A skin lesion imaged with a dermatoscope, a female patient about 60 years old:
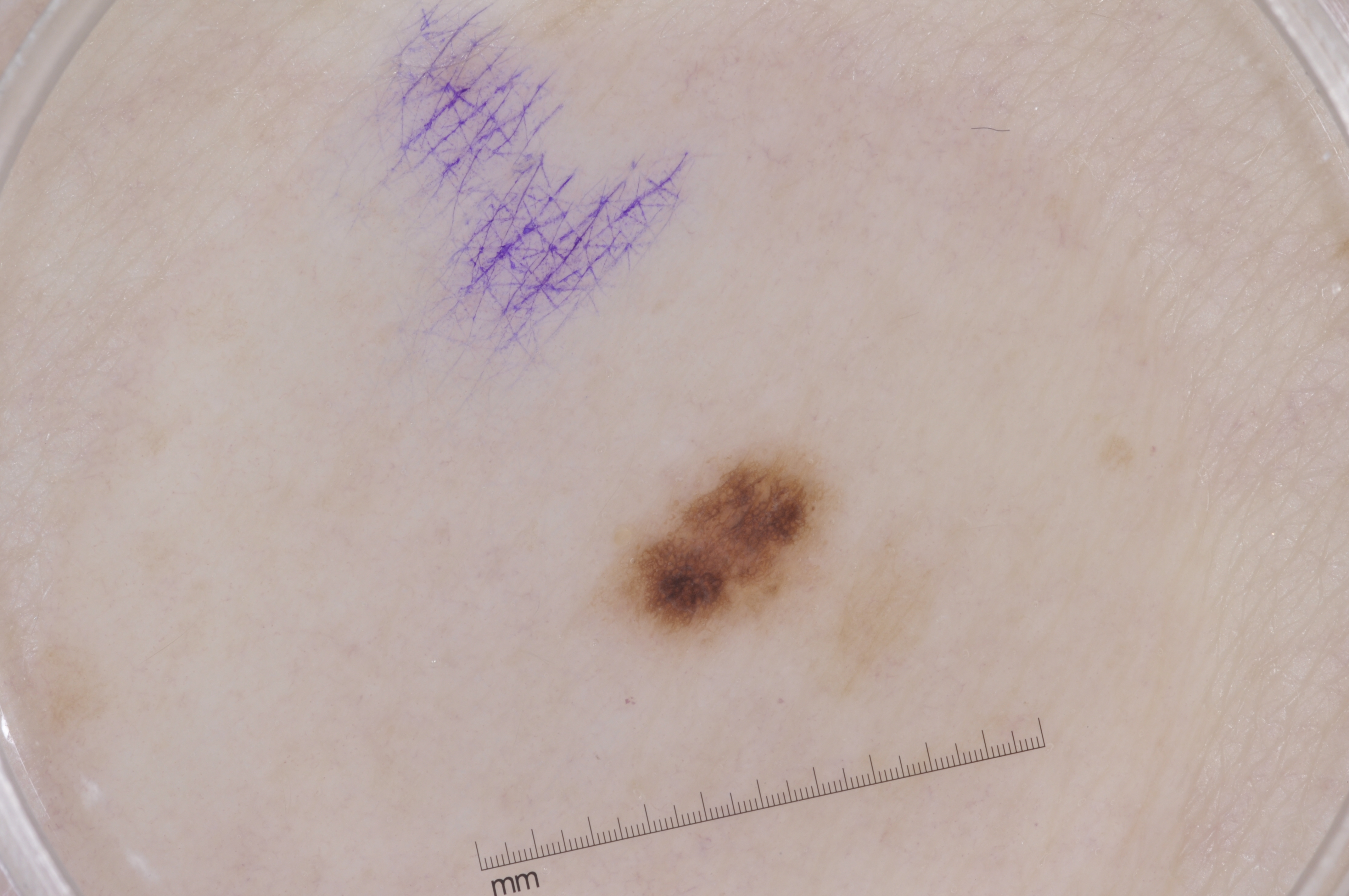Dermoscopic examination shows pigment network, with no negative network, streaks, or milia-like cysts. The visible lesion spans bbox=[587, 442, 850, 653]. The lesion takes up about 3% of the image. The clinical diagnosis was a melanocytic nevus.